A clinical close-up photograph of a skin lesion:
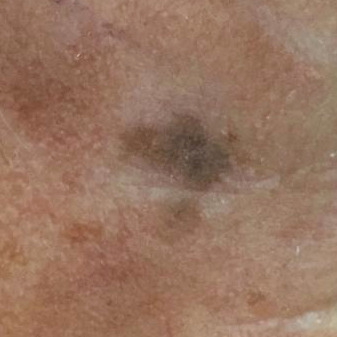The lesion is located on the face.
The patient reports that the lesion is not elevated.
Consistent with a benign skin lesion — a seborrheic keratosis.